The lesion involves the leg, palm, back of the torso, front of the torso, head or neck, back of the hand and arm. The patient is a male aged 70–79. An image taken at an angle.
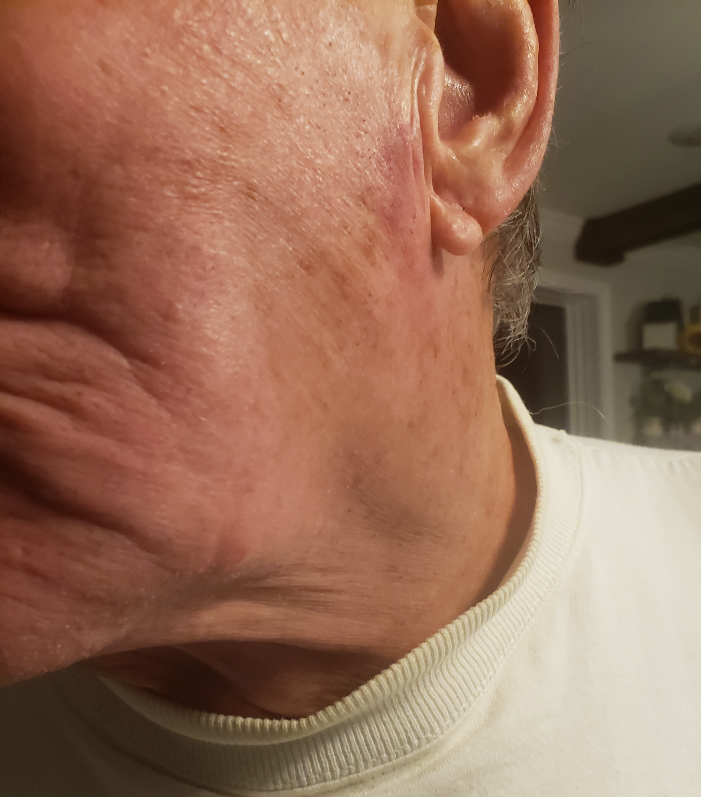assessment: favoring Seborrheic Dermatitis; an alternative is Psoriasis; possibly Allergic Contact Dermatitis.